A dermoscopic image of a skin lesion: 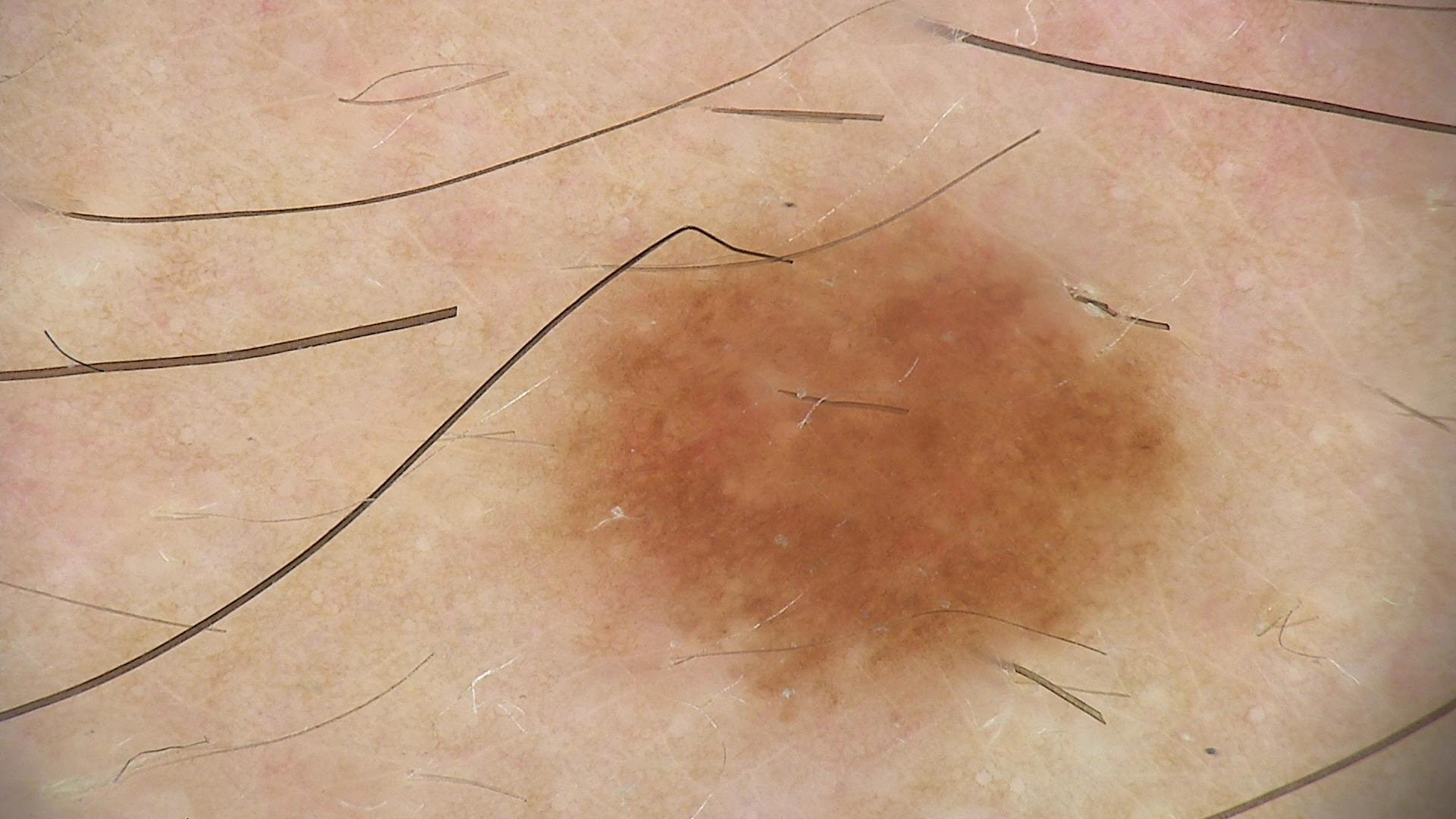Consistent with a benign lesion — a dysplastic junctional nevus.